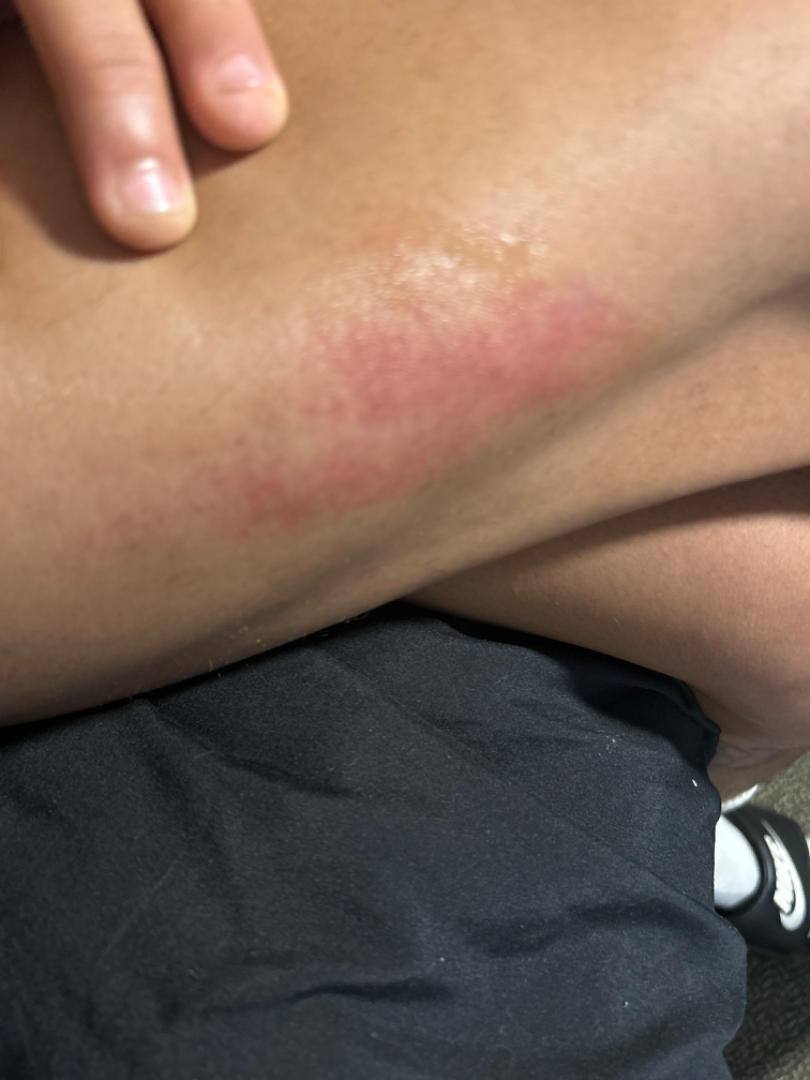Q: Anatomic location?
A: leg
Q: When did this start?
A: less than one week
Q: Who is the patient?
A: male, age 18–29
Q: Reported symptoms?
A: itching and burning
Q: What is the framing?
A: at an angle
Q: Patient's own categorization?
A: skin that appeared healthy to them
Q: What is the dermatologist's impression?
A: the impression was split between Insect Bite; ecchymoses; and Acute dermatitis, NOS